A close-up photograph — 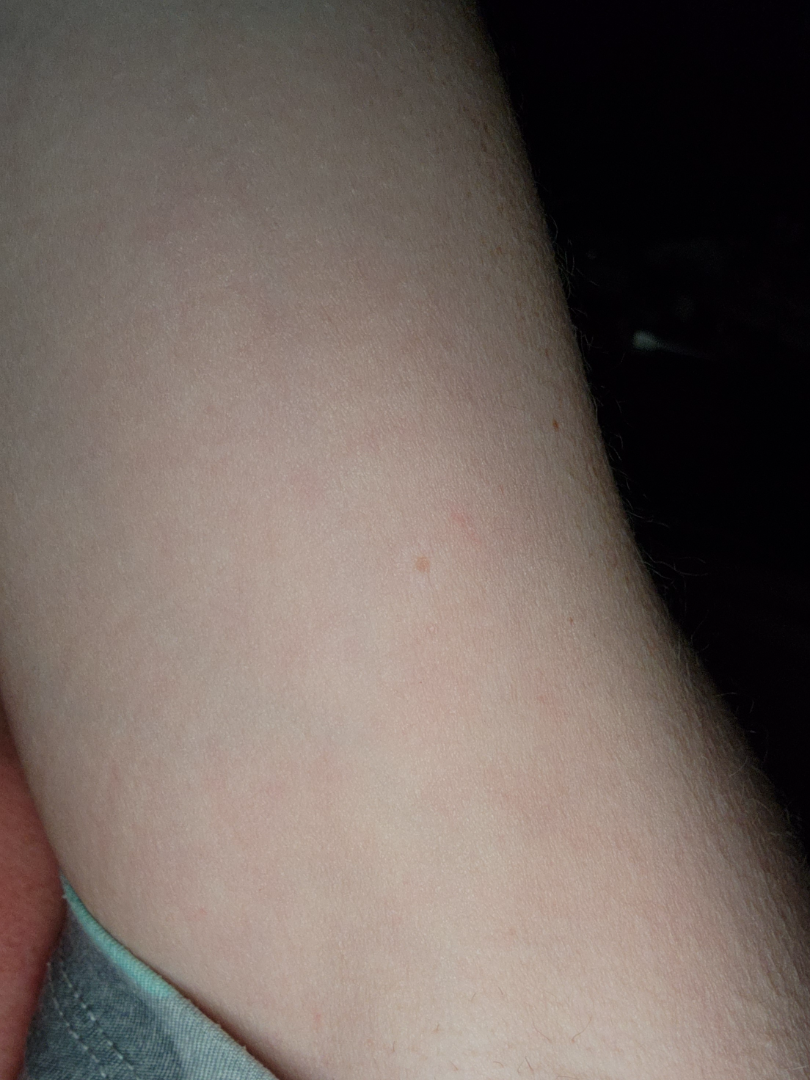On photographic review: Allergic Contact Dermatitis (possible); Irritant Contact Dermatitis (possible).